A male subject aged 38 to 42 · a dermoscopy image of a single skin lesion: 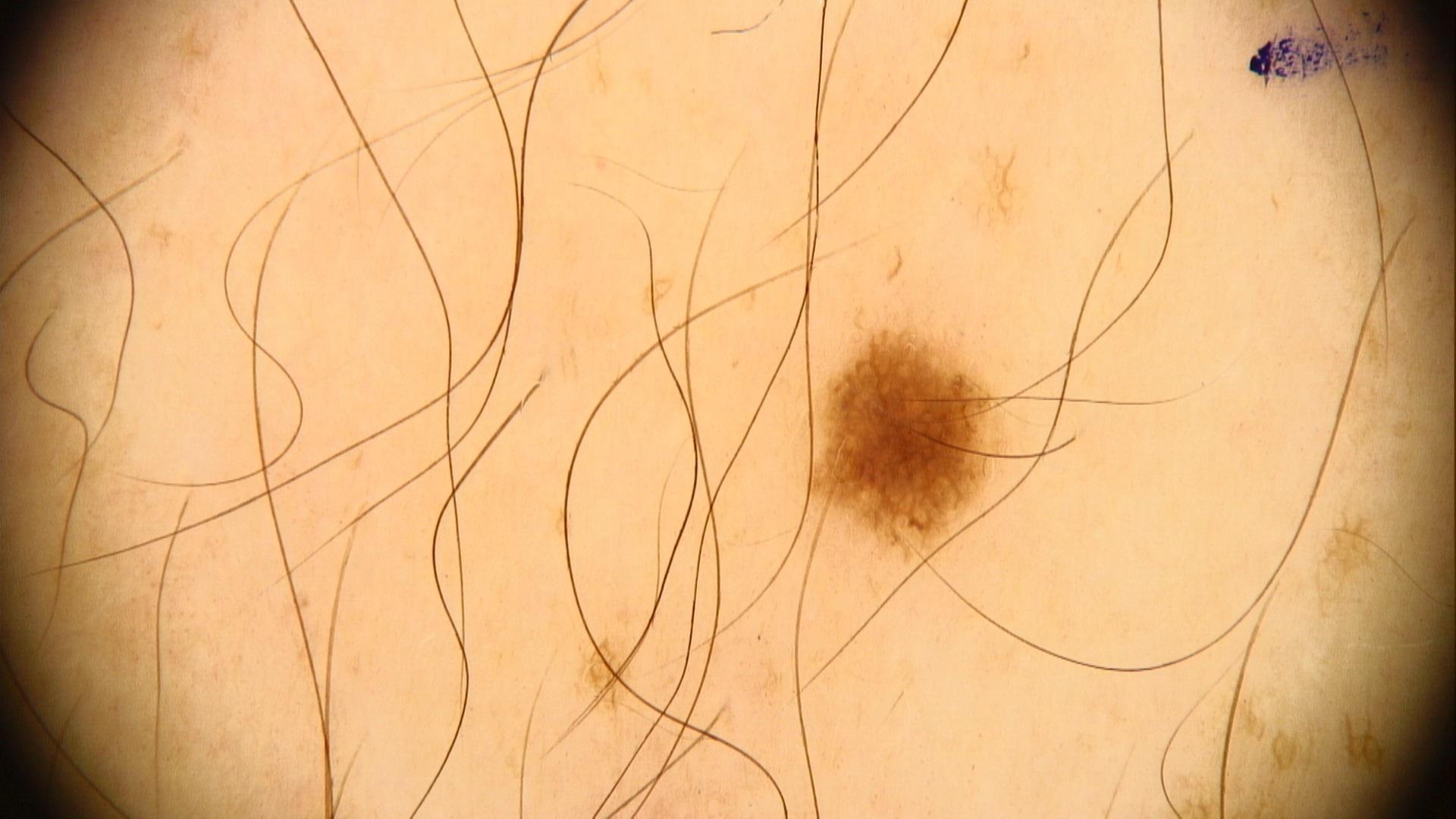The lesion is located on the trunk. The clinical assessment was a lesion of melanocytic origin — a nevus.